Located on the front of the torso; the patient is 40–49, female; an image taken at an angle: 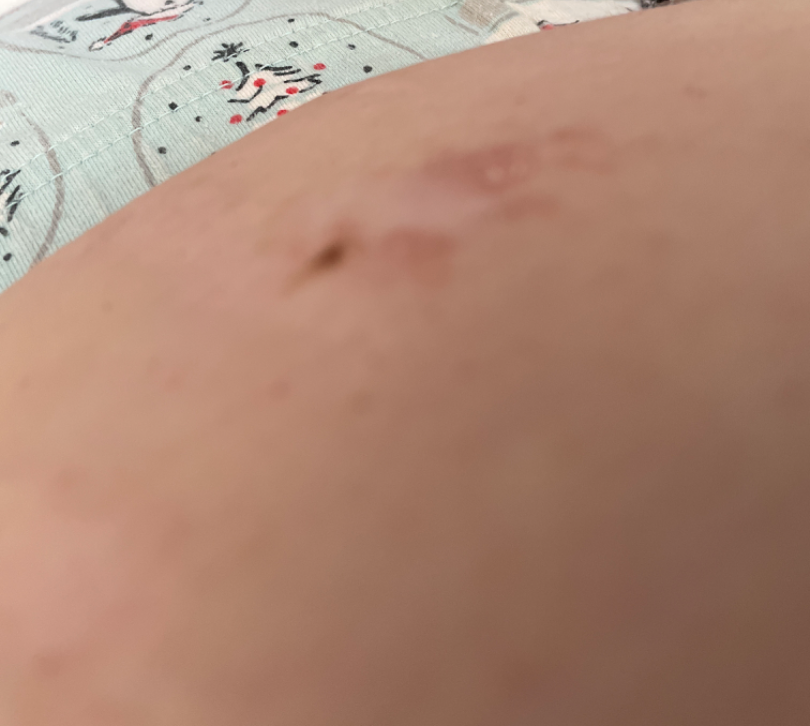The case was difficult to assess from the available photograph.